A dermoscopy image of a single skin lesion.
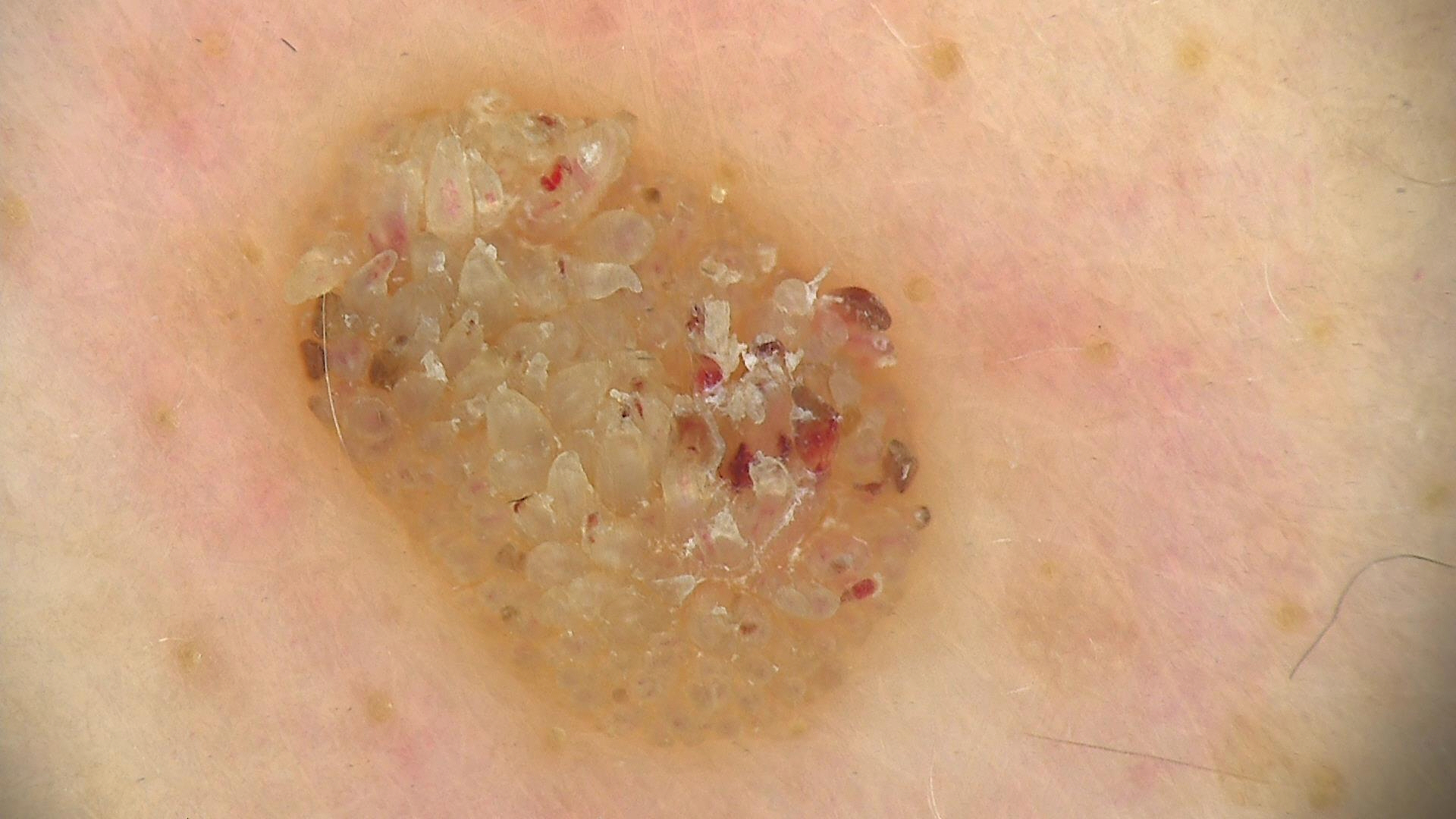Summary: The morphology is that of a keratinocytic lesion. Impression: Diagnosed as a seborrheic keratosis.